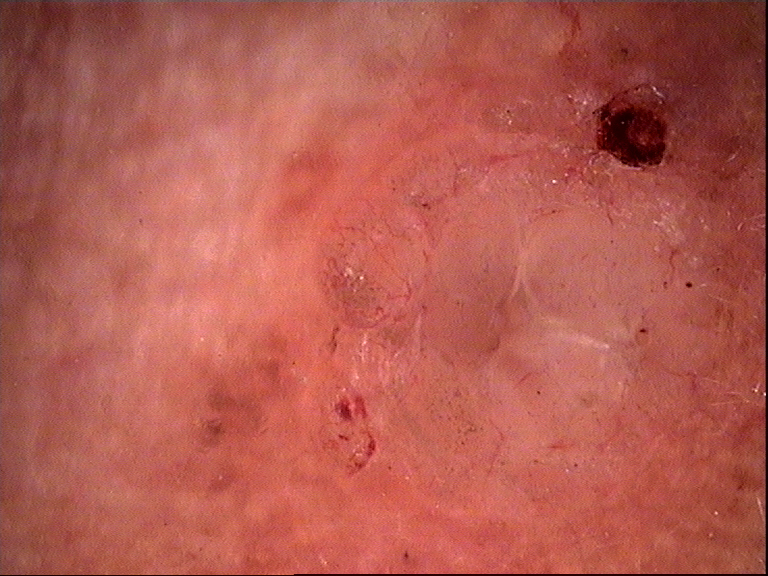class = basal cell carcinoma (biopsy-proven)